Close-up view: 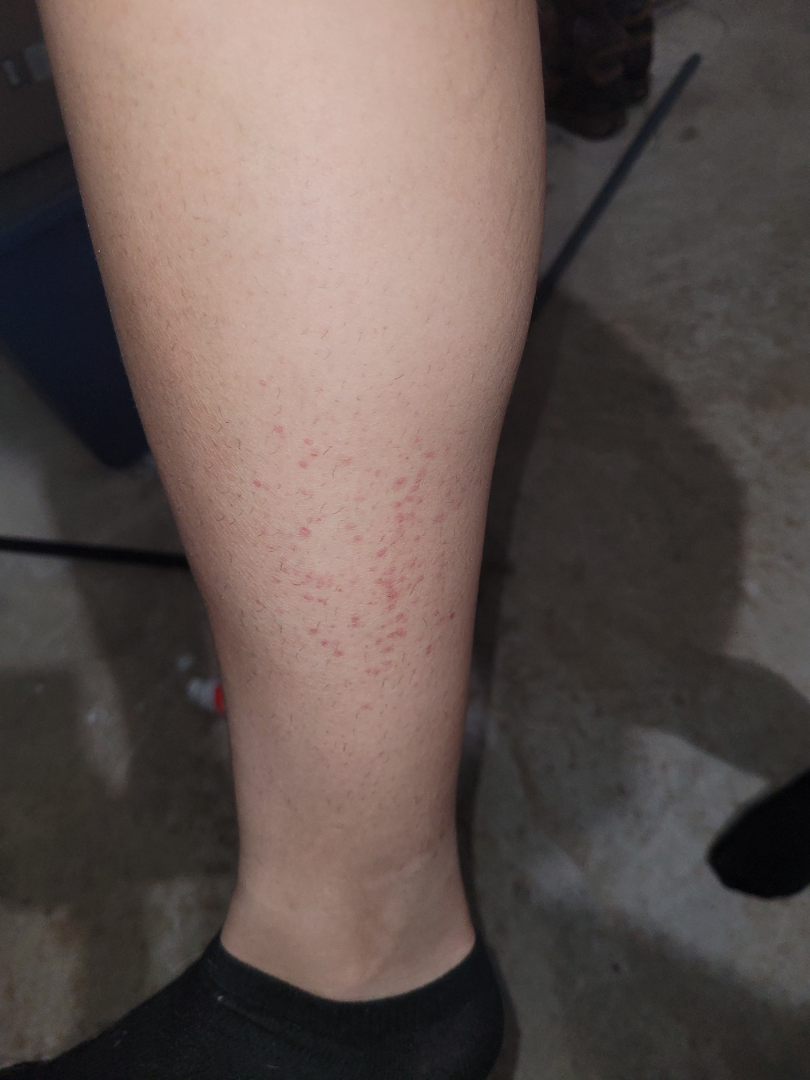Case summary:
• differential diagnosis: the leading impression is Pigmented purpuric eruption; possibly Vasculitis of the skin